The condition has been present for less than one week · the affected area is the arm · symptoms reported: bothersome appearance and itching · texture is reported as raised or bumpy · associated systemic symptoms include fatigue · self-categorized by the patient as a rash · the patient is 50–59, female · this image was taken at a distance — 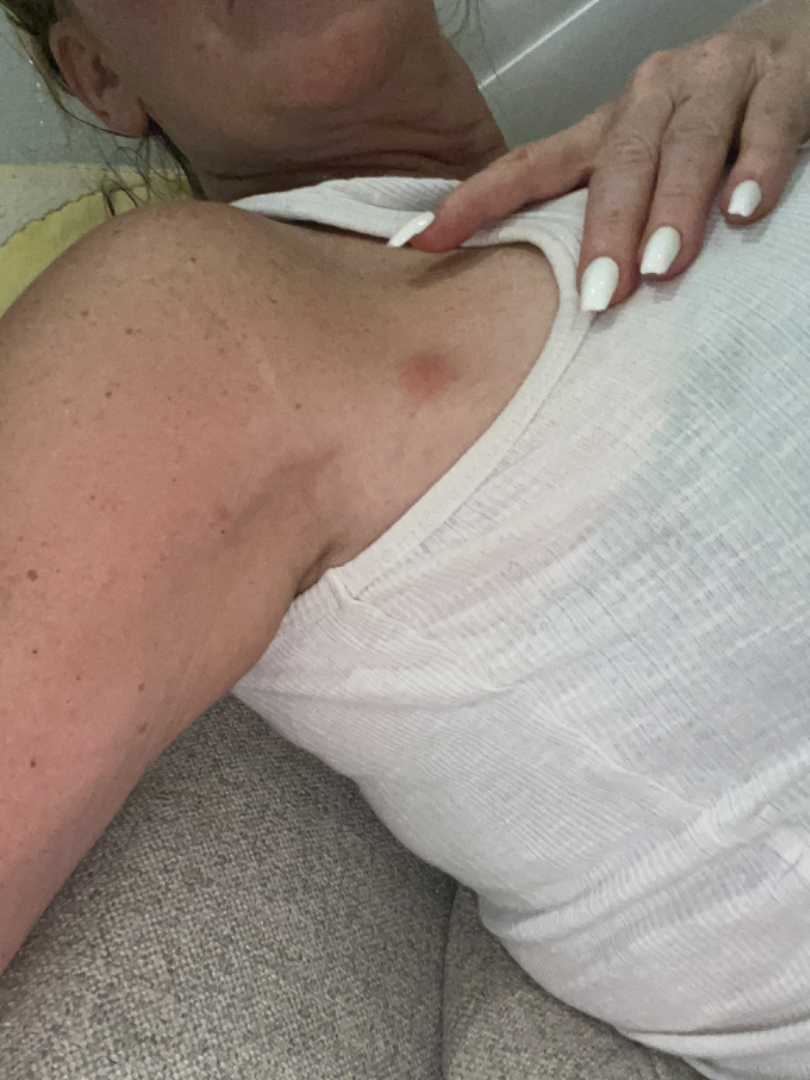Q: What is the differential diagnosis?
A: most consistent with Abscess